A dermoscopic image of a skin lesion: 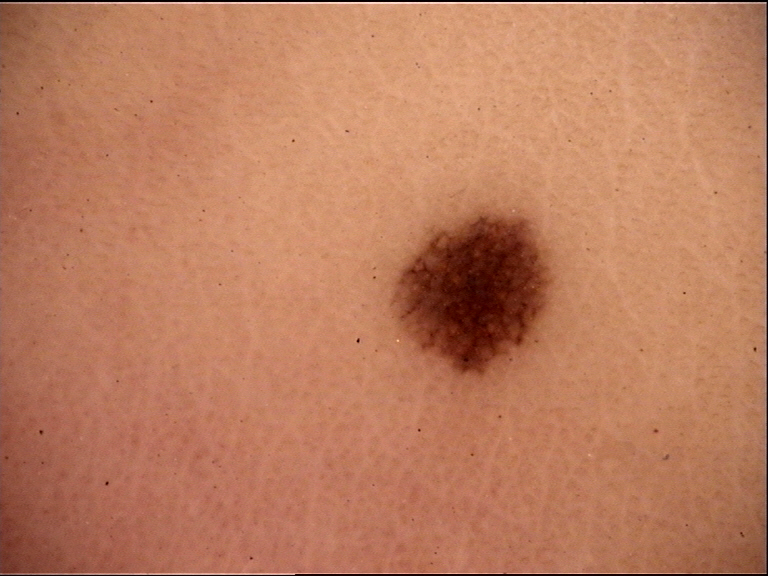subtype=banal
diagnosis=junctional nevus (expert consensus)